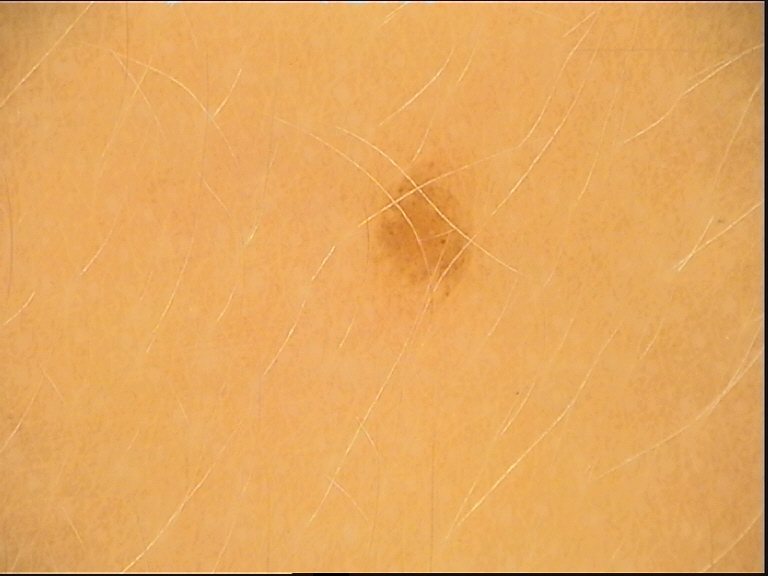{
  "image": "dermatoscopy",
  "diagnosis": {
    "name": "dysplastic junctional nevus",
    "code": "jd",
    "malignancy": "benign",
    "super_class": "melanocytic",
    "confirmation": "expert consensus"
  }
}